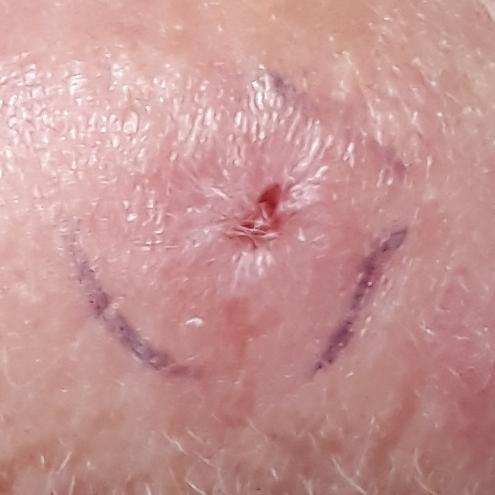| field | value |
|---|---|
| patient | female, 78 years old |
| image | smartphone clinical photo |
| site | the face |
| patient-reported symptoms | pain, bleeding, itching, elevation / no growth, no change in appearance |
| diagnosis | actinic keratosis (biopsy-proven) |